A dermoscopic image of a skin lesion · a female patient, aged around 55 — 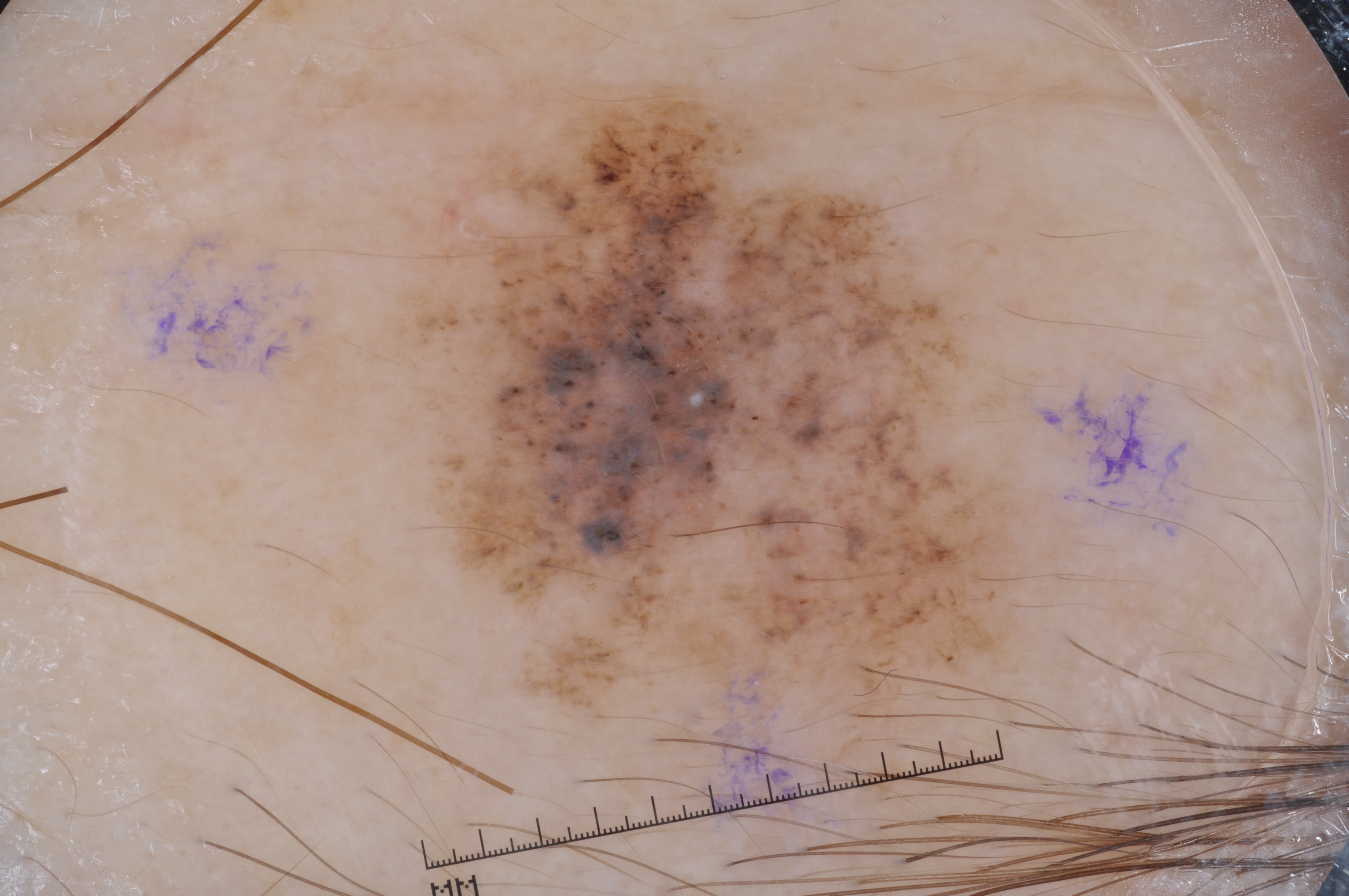Q: Lesion extent?
A: large
Q: Which dermoscopic features were noted?
A: milia-like cysts; absent: negative network, pigment network, and streaks
Q: Where is the lesion located?
A: left=367, top=75, right=1072, bottom=801
Q: What did the assessment conclude?
A: a melanoma